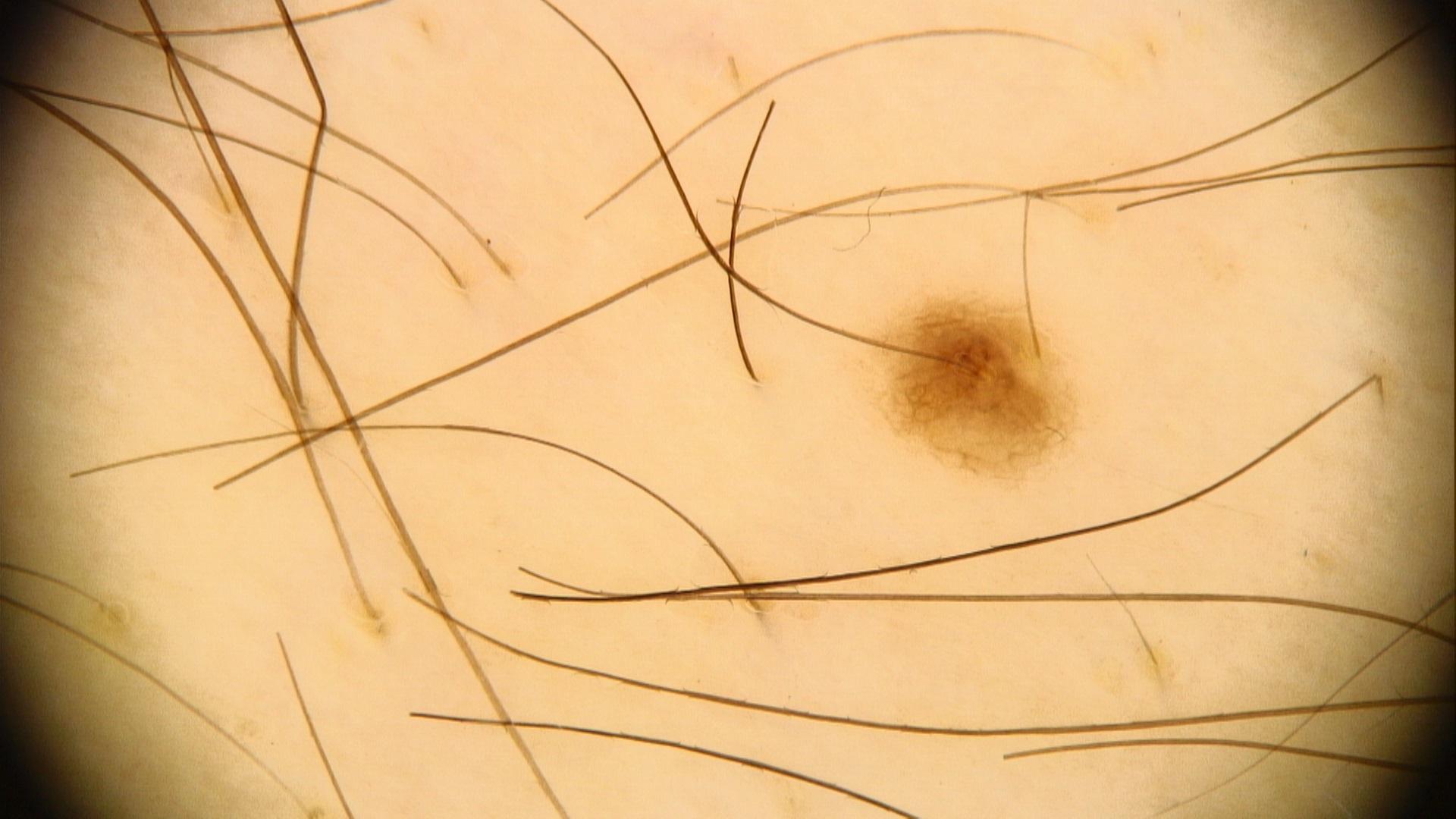Image and clinical context:
A male patient aged 38 to 42. The patient is Fitzpatrick phototype III. A dermoscopic photograph of a skin lesion. The lesion is on a lower extremity.
Impression:
Expert review favored a benign, melanocytic lesion — a nevus.